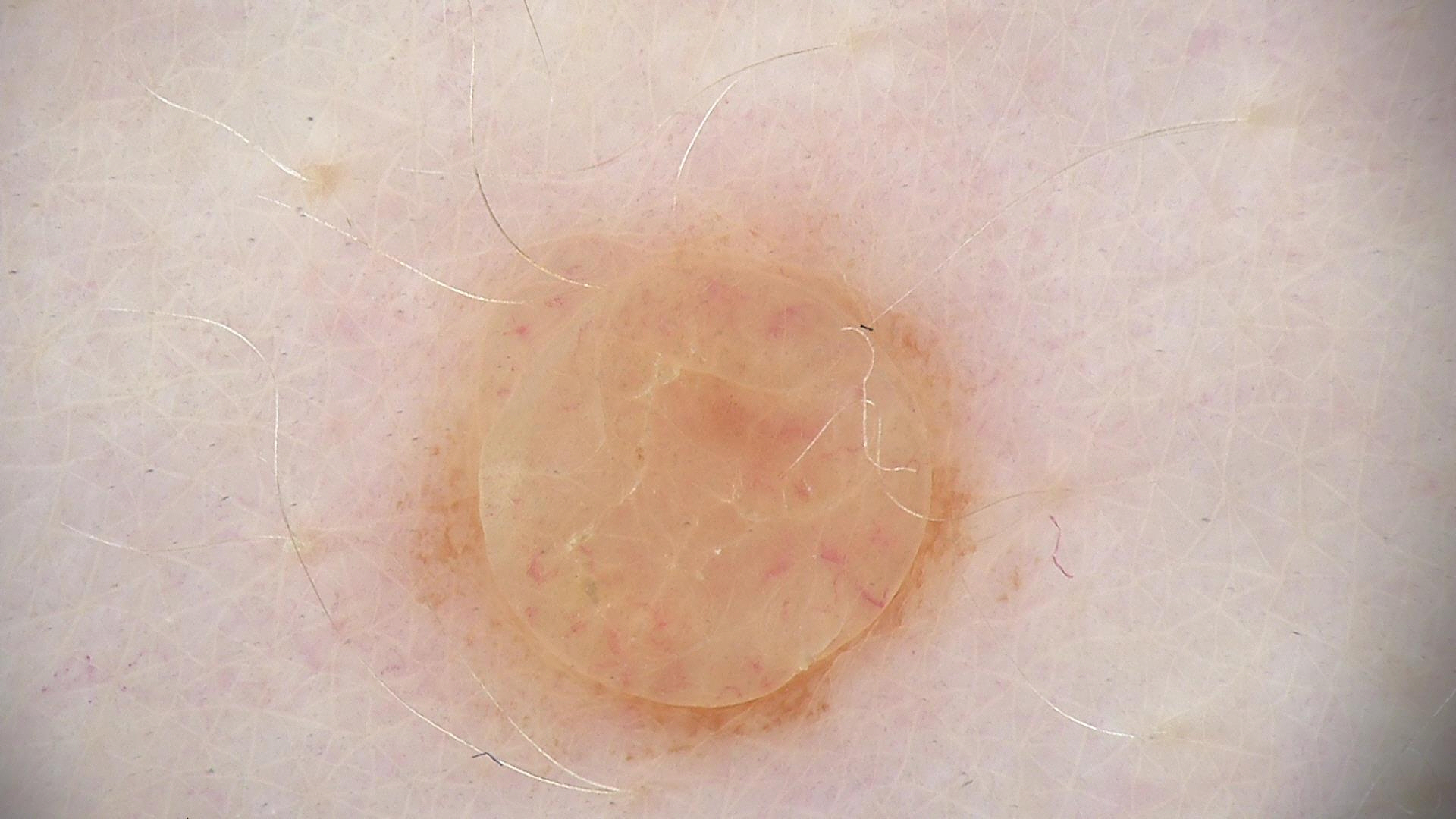class = dermal nevus (expert consensus).